A skin lesion imaged with a dermatoscope · the patient is a female approximately 55 years of age.
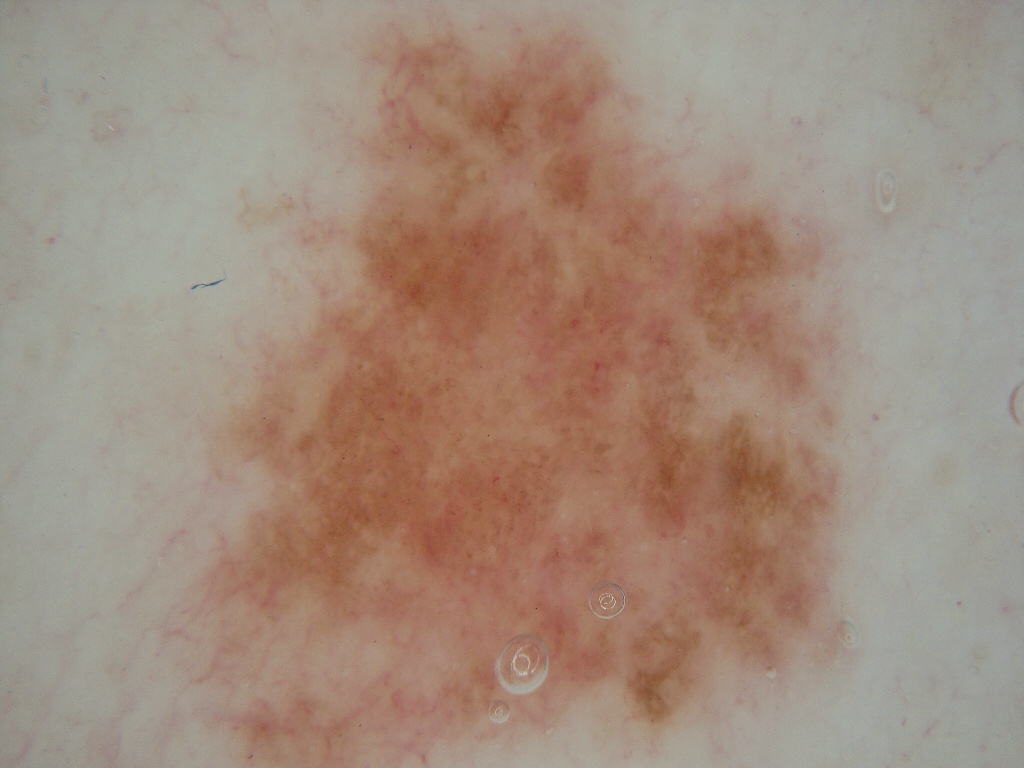As (left, top, right, bottom), the visible lesion spans box(173, 4, 882, 766).
Dermoscopic assessment notes pigment network, with no streaks, negative network, or milia-like cysts.
The clinical diagnosis was a melanocytic nevus, a benign lesion.